Dermoscopy of a skin lesion: 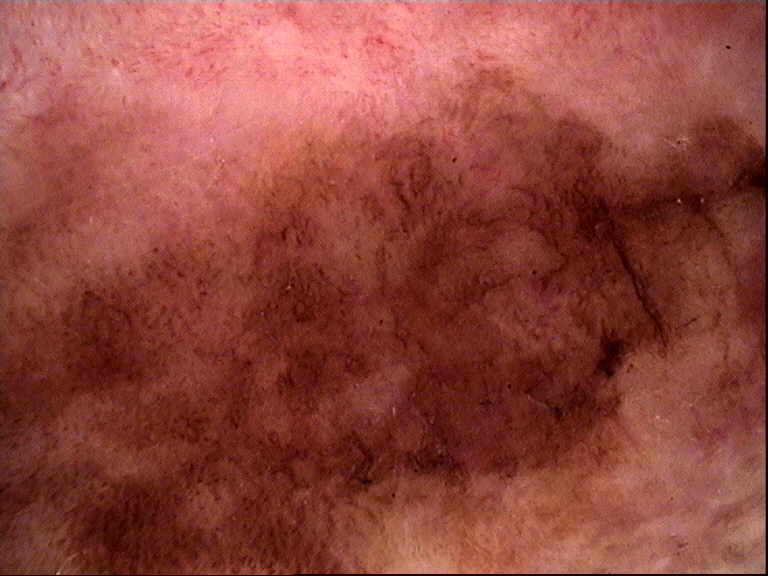{"diagnosis": {"name": "Bowen's disease", "code": "bd", "malignancy": "malignant", "super_class": "non-melanocytic", "confirmation": "histopathology"}}